A dermoscopy image of a single skin lesion.
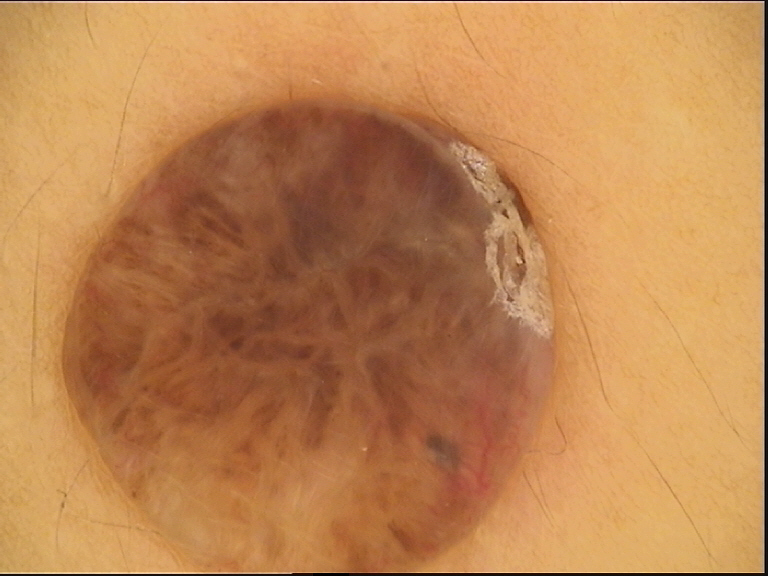The morphology is that of a banal lesion.
Consistent with a dermal nevus.